By history, alcohol use · a clinical photograph showing a skin lesion · the patient is Fitzpatrick skin type II: 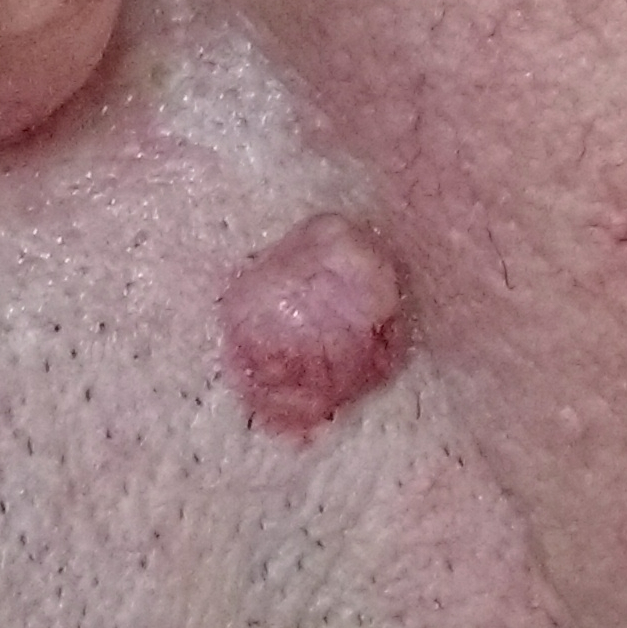  lesion_location: the face
  lesion_size:
    diameter_1_mm: 9.0
    diameter_2_mm: 6.0
  symptoms:
    present:
      - elevation
      - growth
    absent:
      - itching
      - pain
  diagnosis:
    name: basal cell carcinoma
    code: BCC
    malignancy: malignant
    confirmation: histopathology